A dermatoscopic image of a skin lesion.
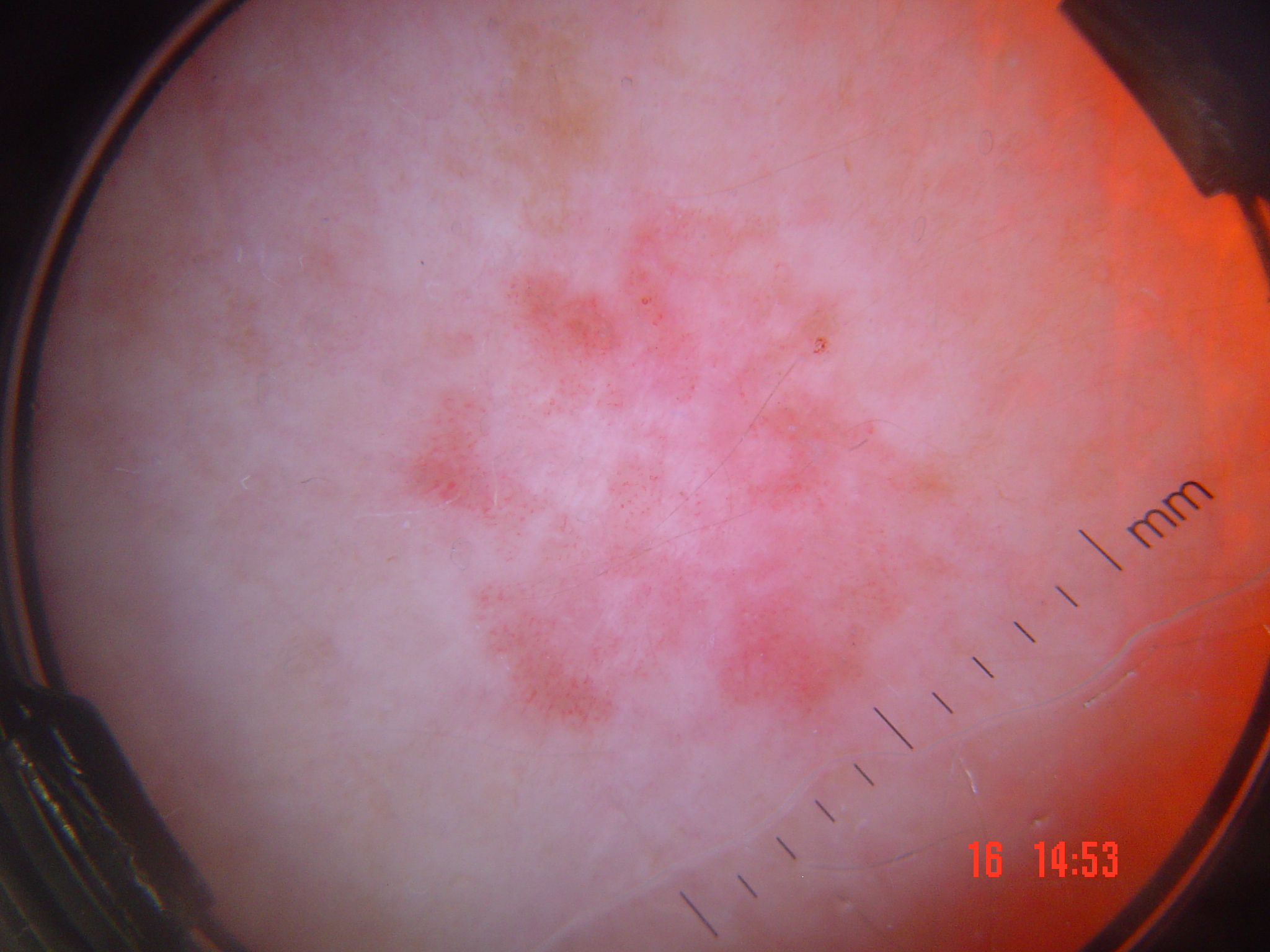Histopathology confirmed a skin cancer — Bowen's disease.